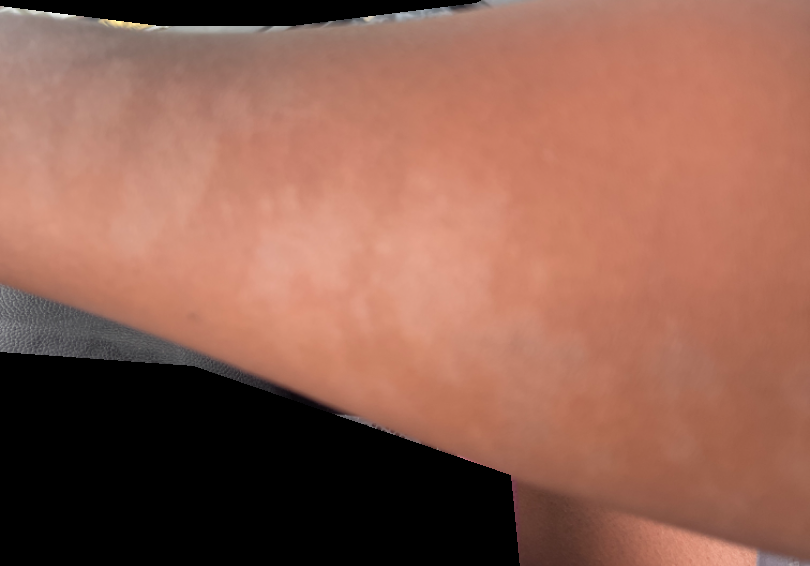subject: female, age 40–49
image framing: at an angle
body site: arm and back of the torso
differential diagnosis: Pityriasis alba and Vitiligo were considered with similar weight; possibly Post-Inflammatory hypopigmentation